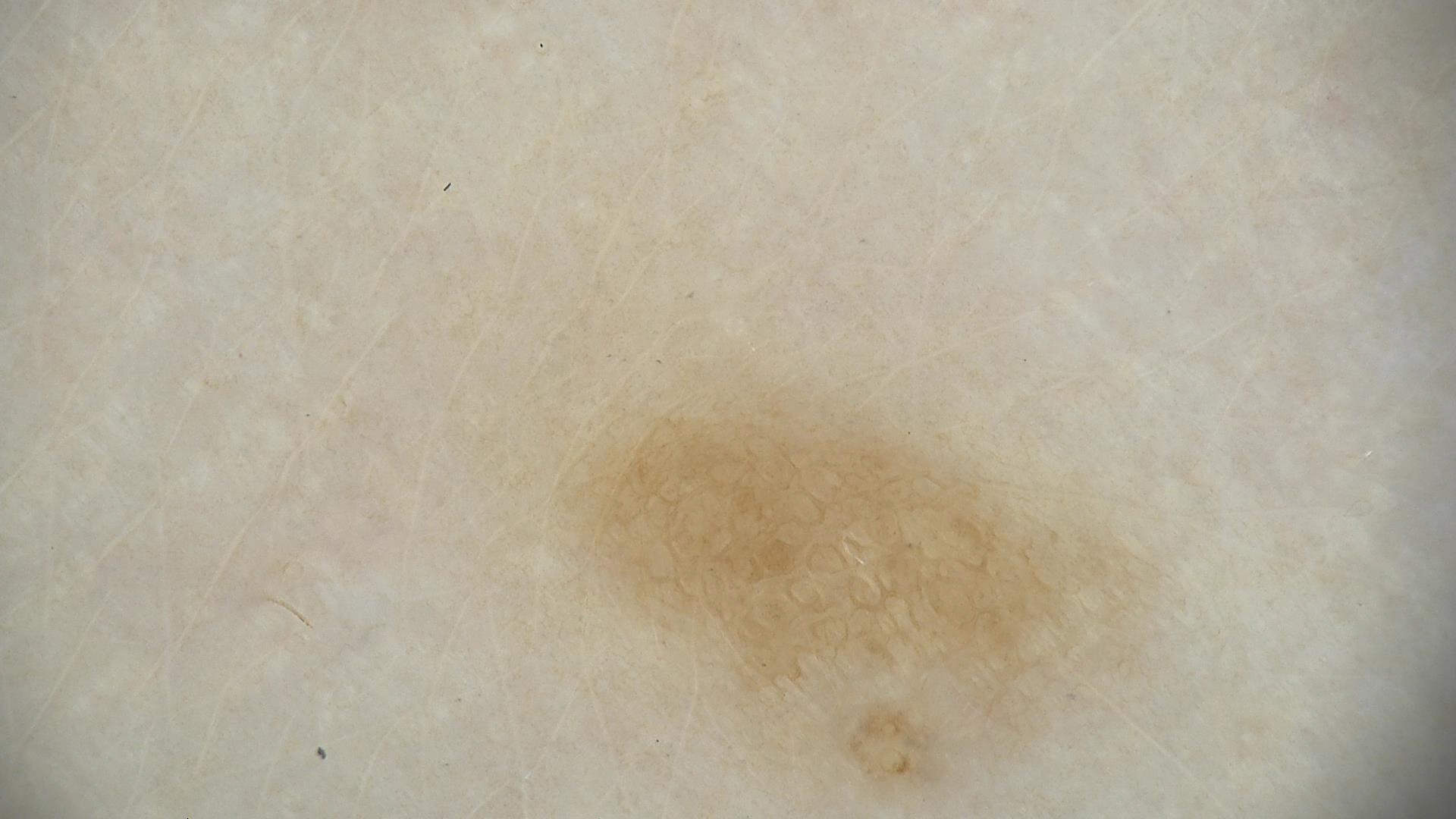Conclusion: Diagnosed as a junctional nevus.